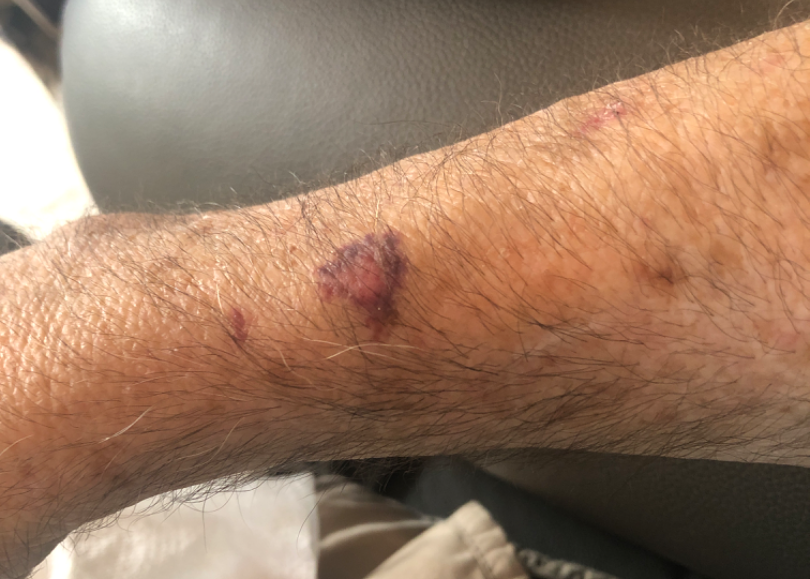affected area: arm
described texture: flat
skin tone: Fitzpatrick skin type III; lay graders estimated Monk skin tone scale 4
symptoms: enlargement
onset: less than one week
framing: close-up
assessment: consistent with ecchymoses